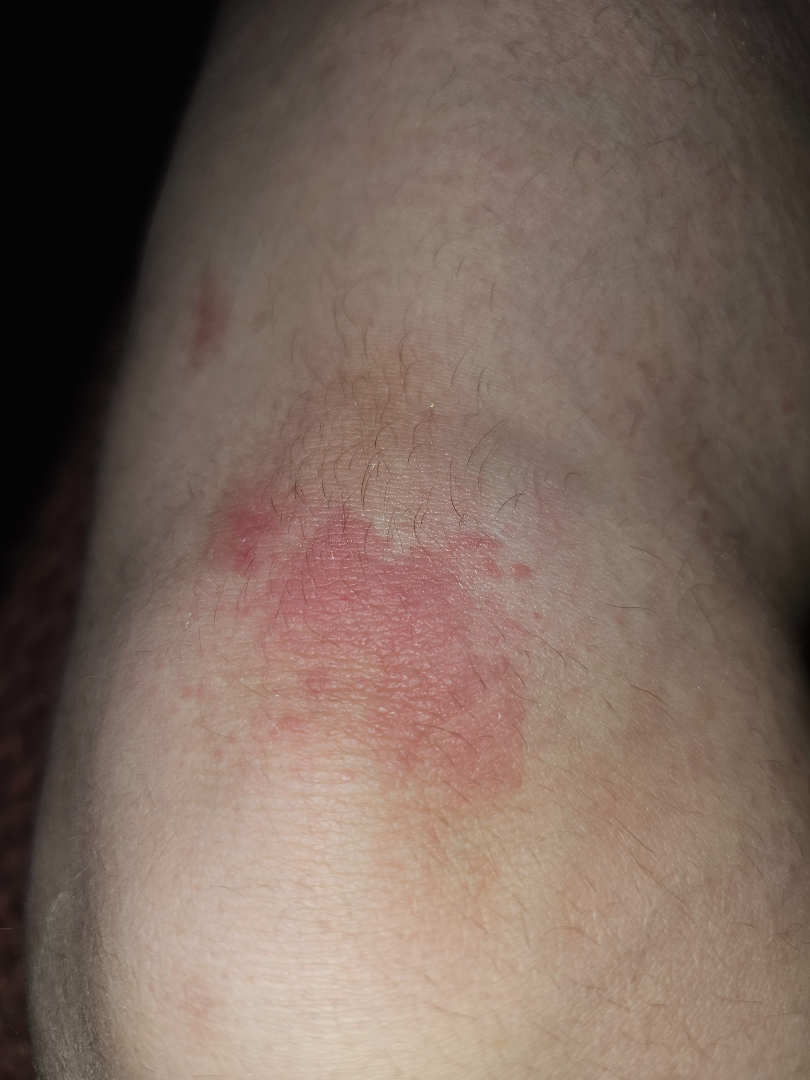- assessment: ungradable on photographic review
- image framing: close-up